A subject aged 50 — 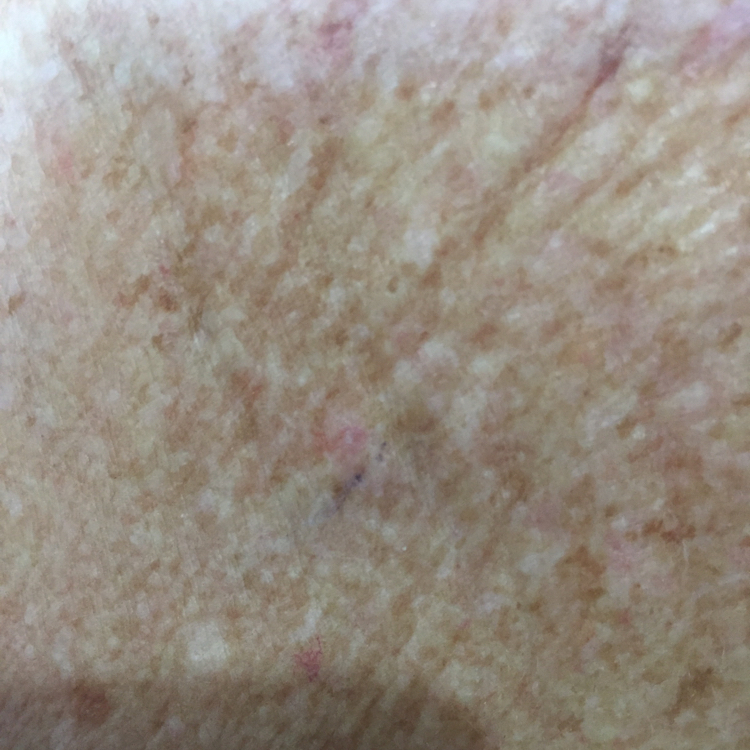Findings: No symptoms reported. Conclusion: Clinically diagnosed as an actinic keratosis.